The patient says their skin tans without first burning. A female patient 78 years of age. Collected as part of a research study, without a referral diagnosis. The patient describes having numerous moles — 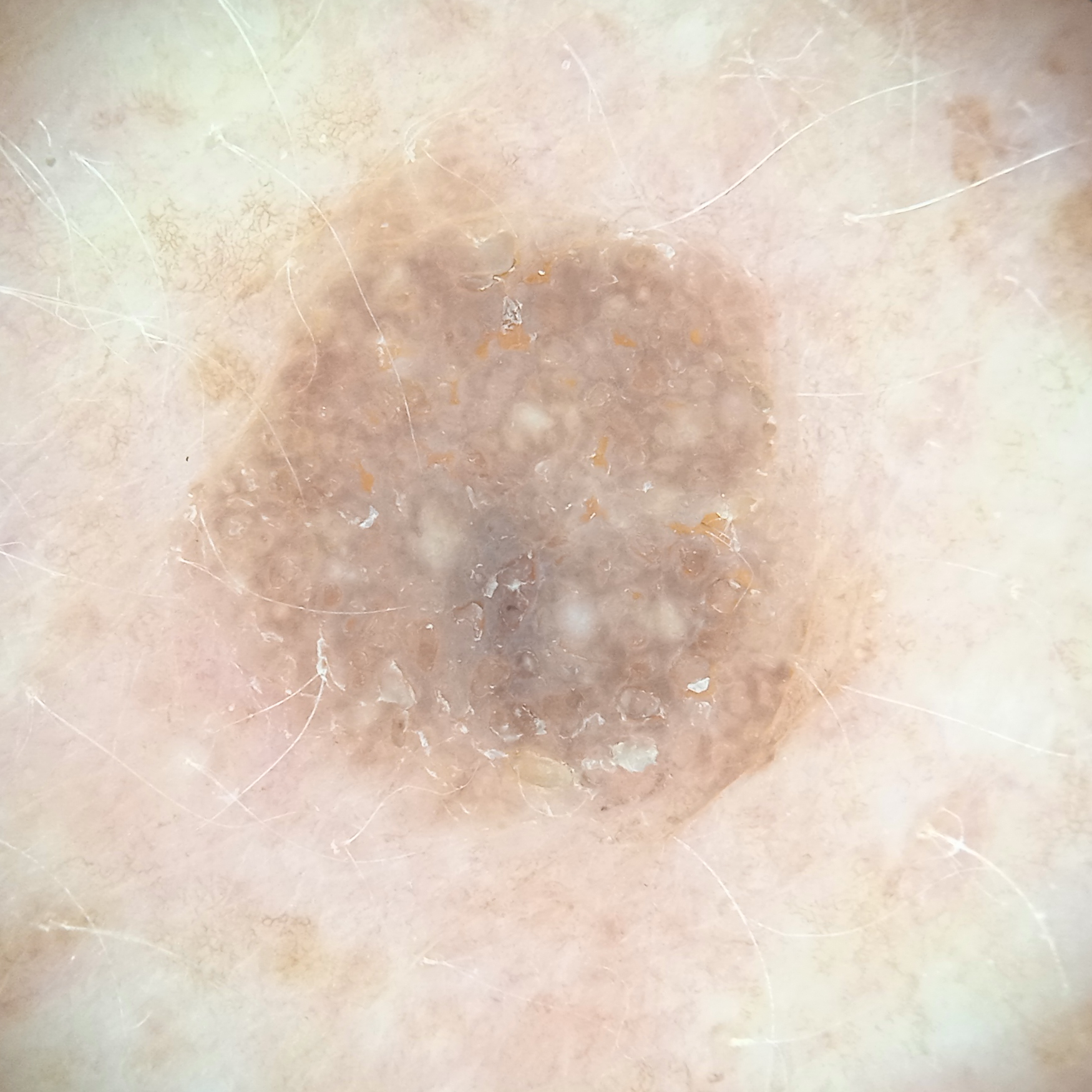The lesion is located on the back. The lesion is about 7.3 mm across. The consensus diagnosis for this lesion was a seborrheic keratosis.